Symptoms reported: itching. Located on the arm, front of the torso and head or neck. Texture is reported as raised or bumpy. This is a close-up image. The subject is 50–59, female:
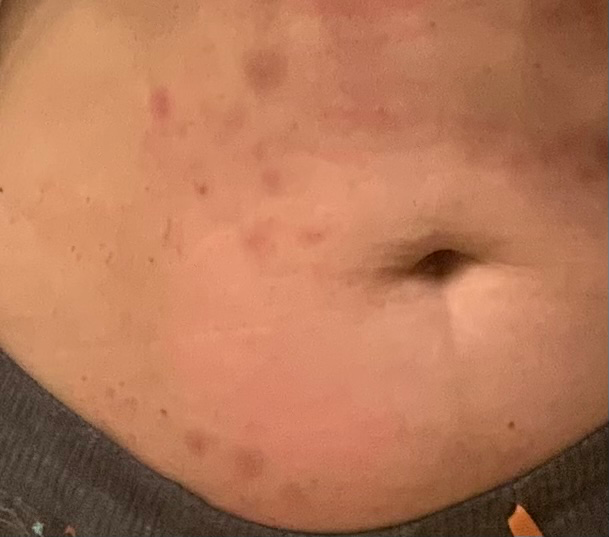assessment: unable to determine.